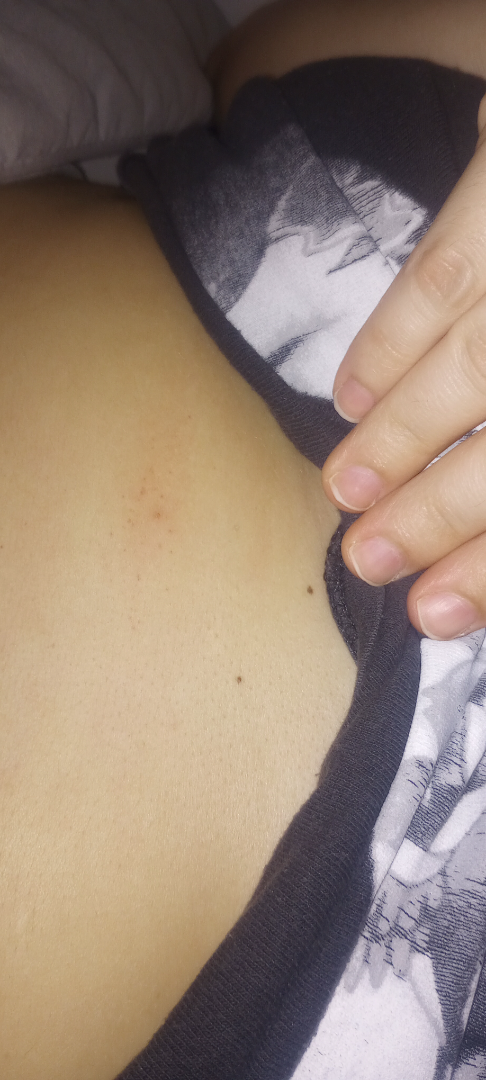<report>
  <assessment>unable to determine</assessment>
</report>